A dermoscopic close-up of a skin lesion.
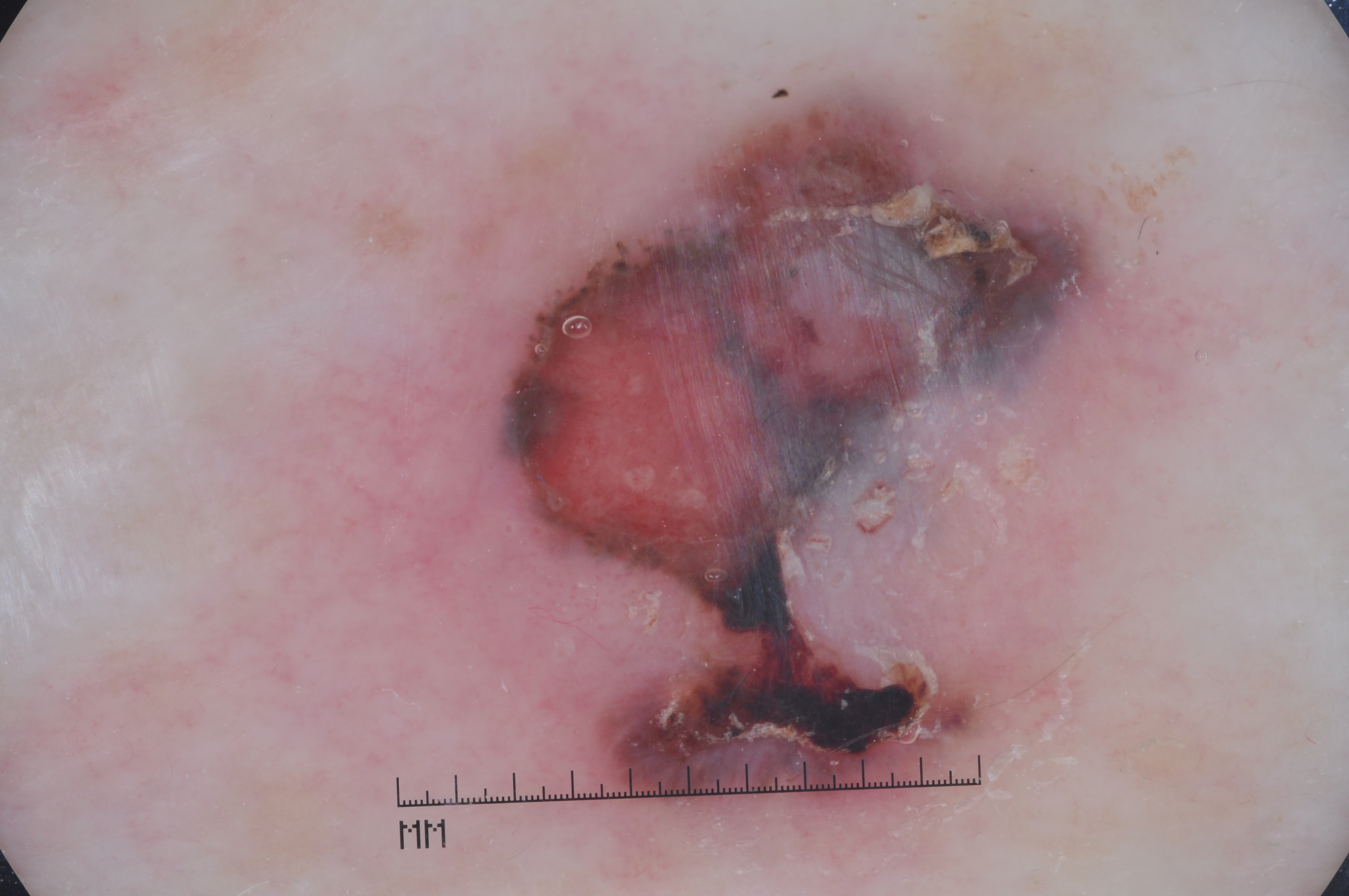features — streaks; absent: pigment network, negative network, and milia-like cysts
lesion location — bbox=[325, 75, 1194, 863]
assessment — a melanoma